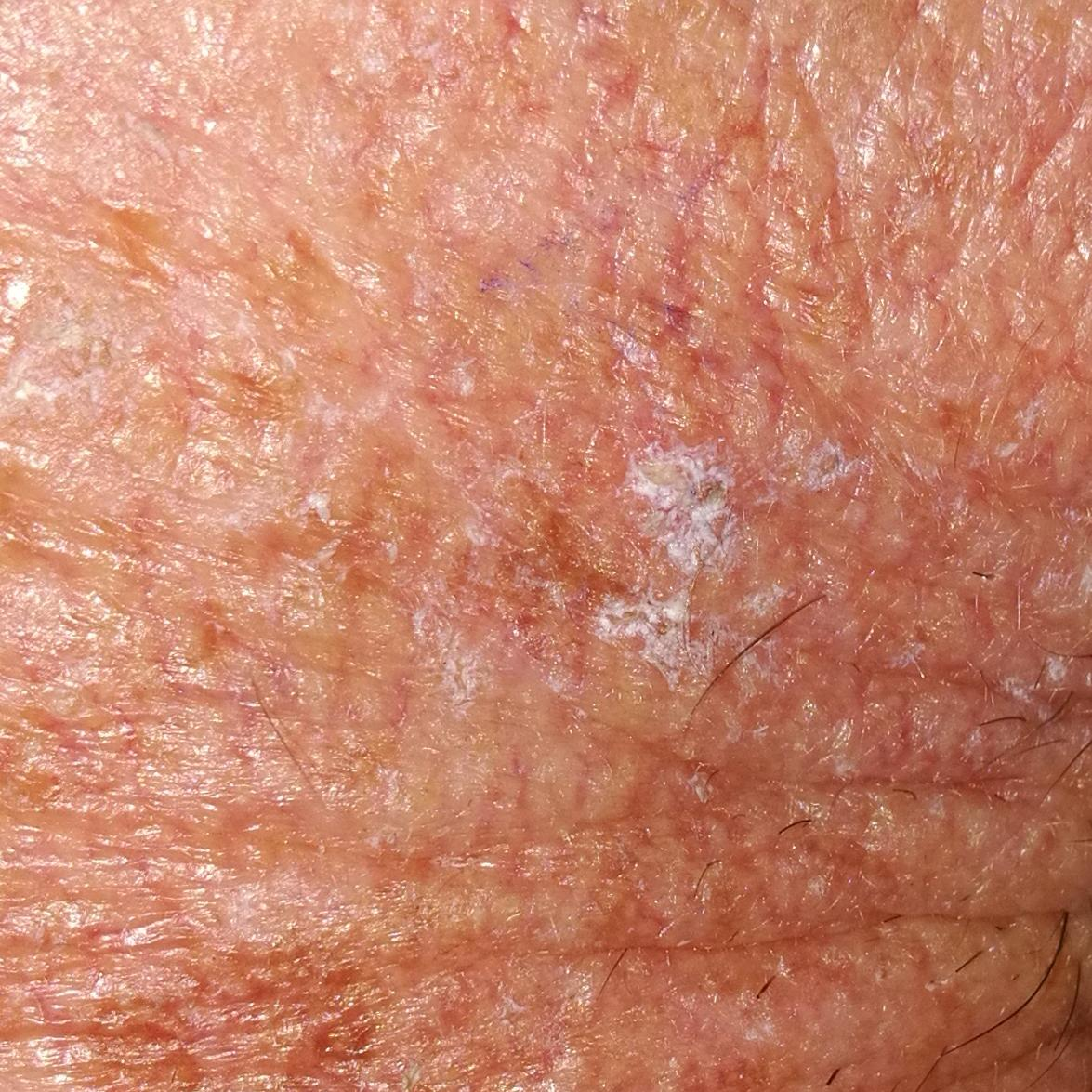Notes:
- image type: clinical photo
- patient: 52 years of age
- body site: the face
- symptoms: itching
- diagnosis: actinic keratosis (clinical consensus)